This is a close-up image; the patient is 40–49, female; the lesion involves the back of the torso.
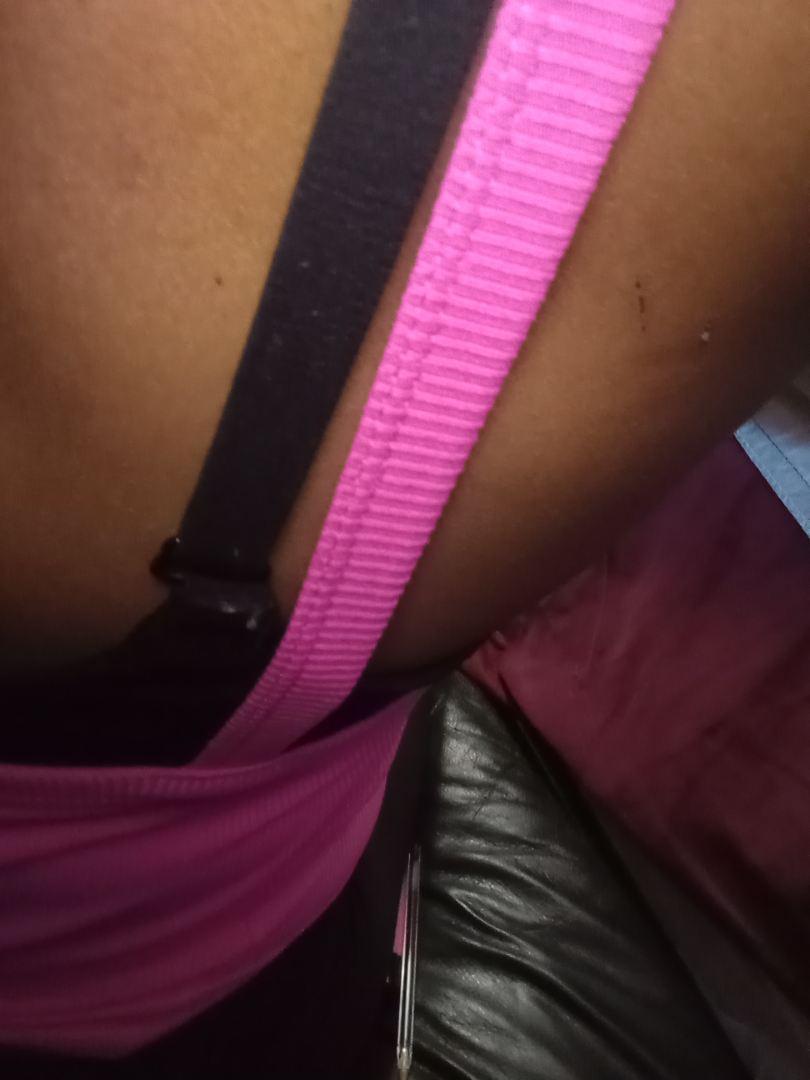{"assessment": "ungradable on photographic review", "patient_category": "a rash", "symptoms": ["itching", "bothersome appearance"], "duration": "one to four weeks", "texture": "rough or flaky", "skin_tone": {"fitzpatrick": "V", "monk_skin_tone": 5}}